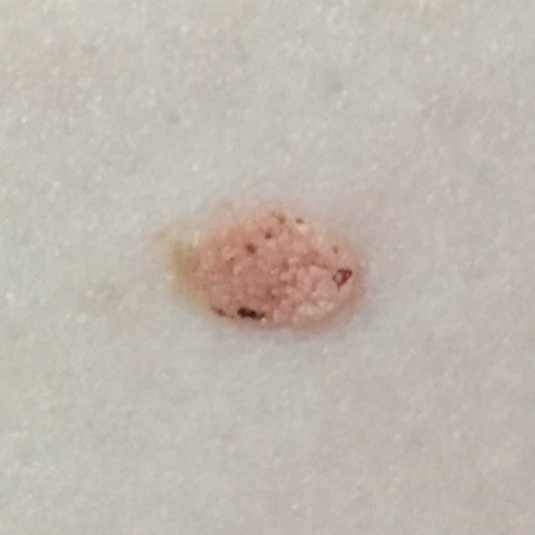Consistent with a seborrheic keratosis.